A dermoscopy image of a single skin lesion.
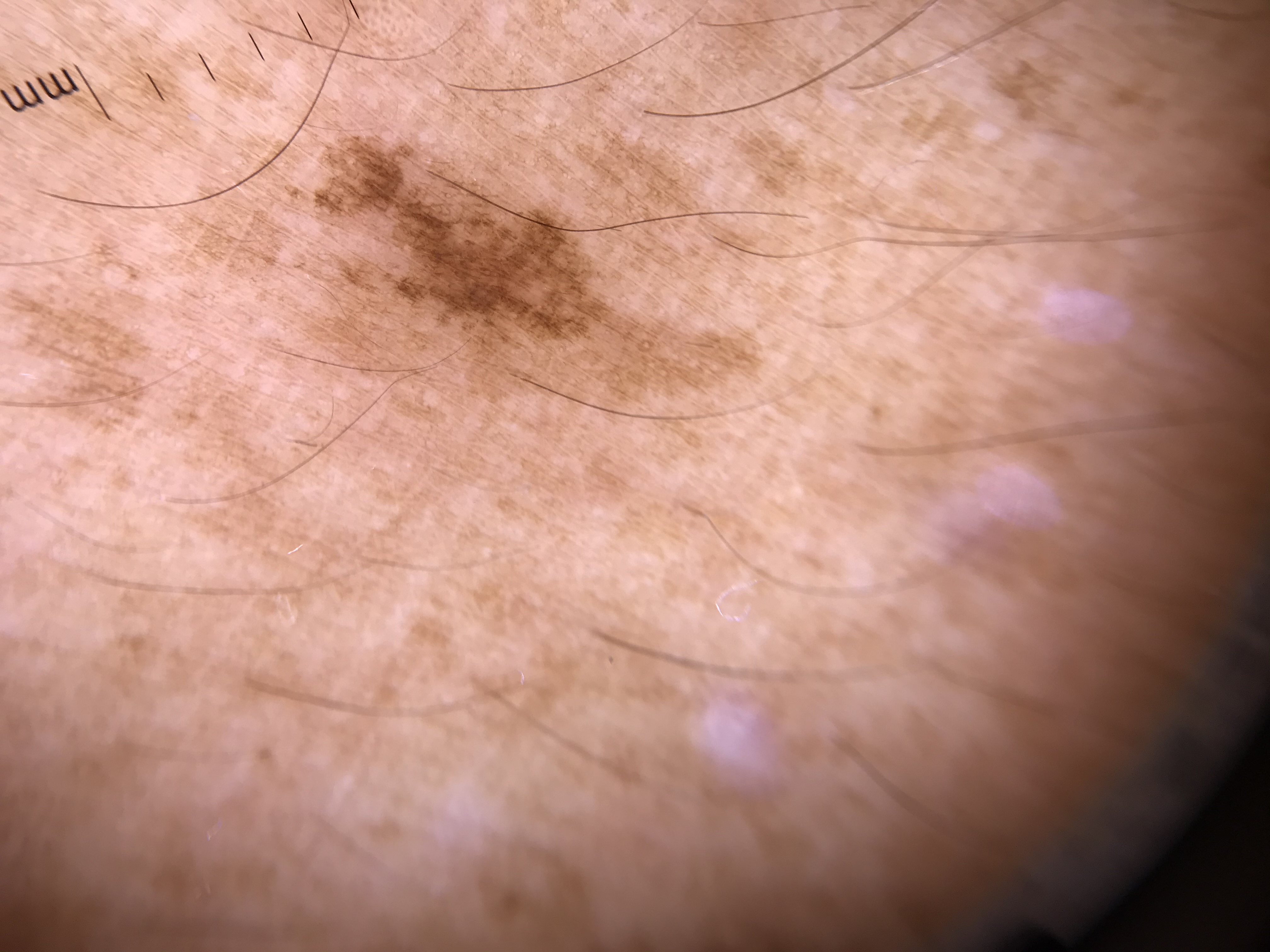Consistent with a solar lentigo.